A dermoscopic image of a skin lesion.
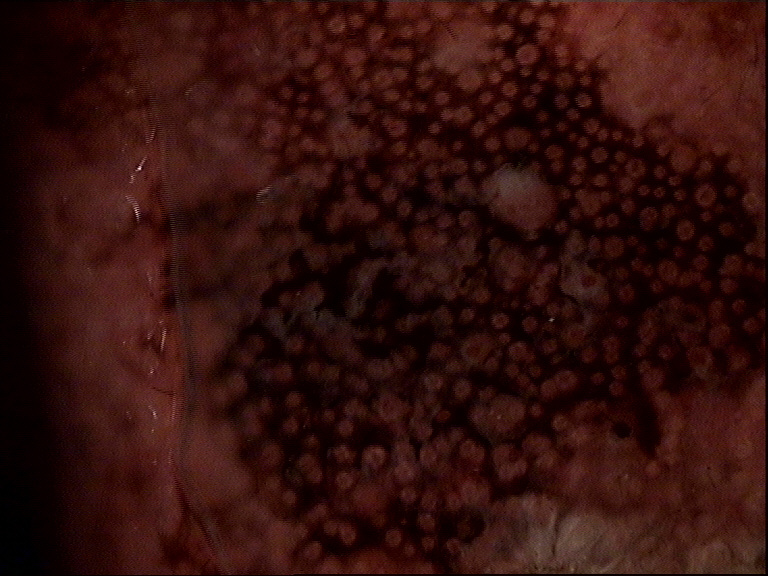Q: What is the diagnosis?
A: lentigo maligna (biopsy-proven)